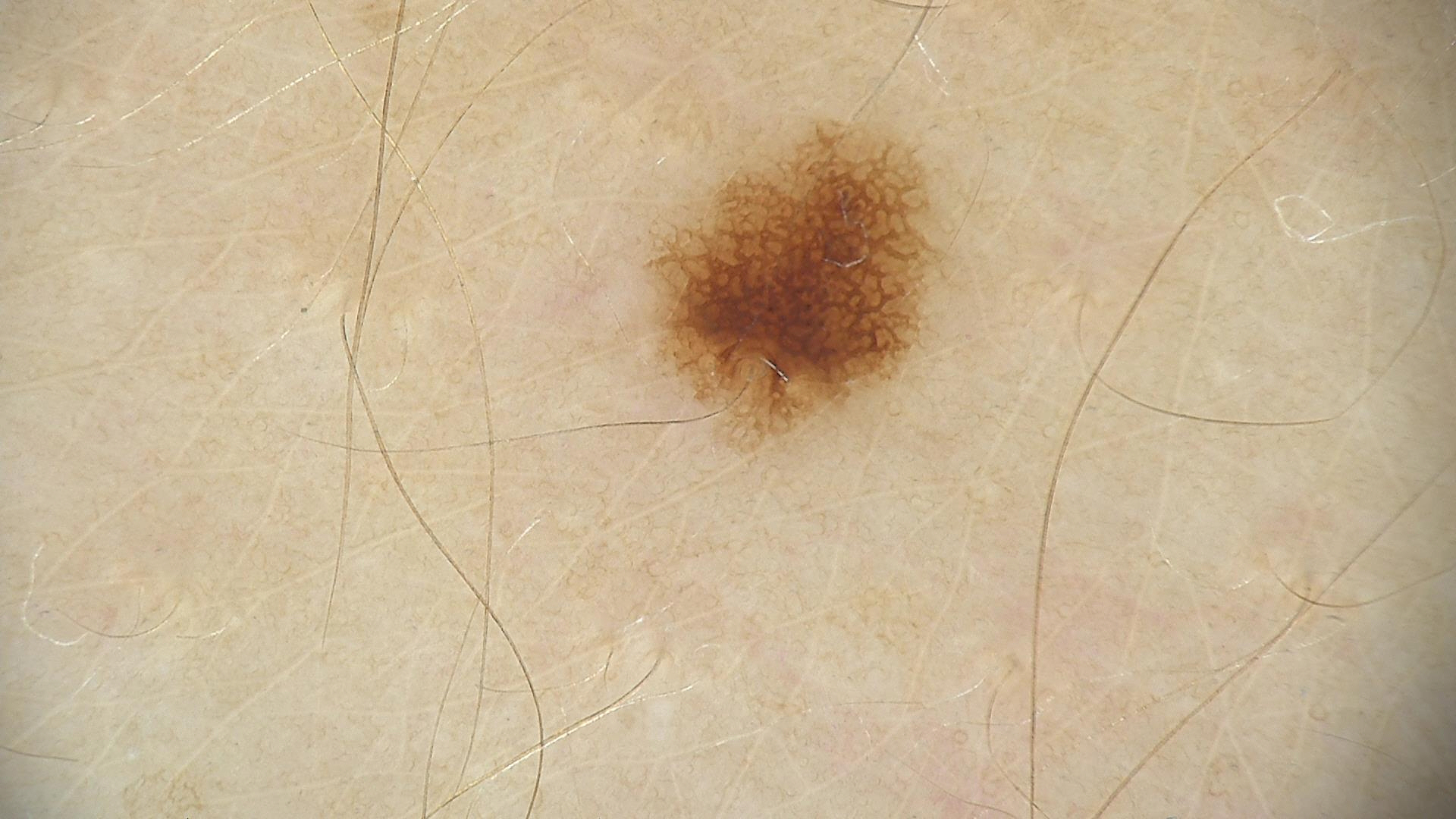label: dysplastic junctional nevus (expert consensus).